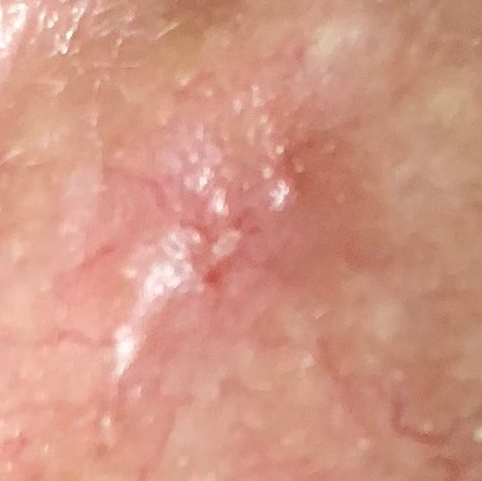A clinical photograph showing a skin lesion. The patient is Fitzpatrick skin type II. The lesion involves the face. The lesion measures approximately 7 × 5 mm. Per patient report, the lesion is elevated, but does not hurt. Histopathology confirmed a malignancy — a basal cell carcinoma.